A female patient in their early 60s. A clinical photograph of a skin lesion. The chart records prior skin cancer (patient or family), tobacco use, prior malignancy (patient or family), no alcohol use, and no pesticide exposure: 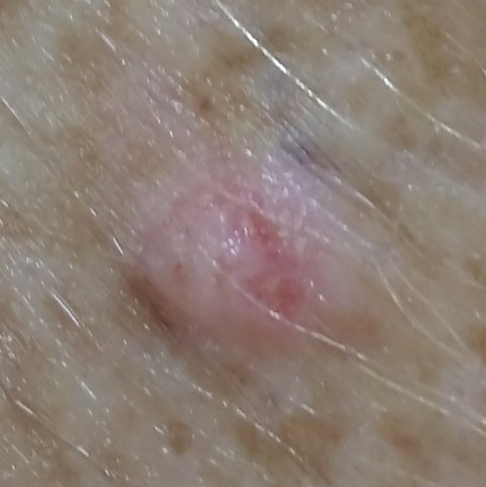The lesion is on a thigh.
The lesion measures 5 × 4 mm.
Per patient report, the lesion is elevated.
Histopathologically confirmed as an actinic keratosis.